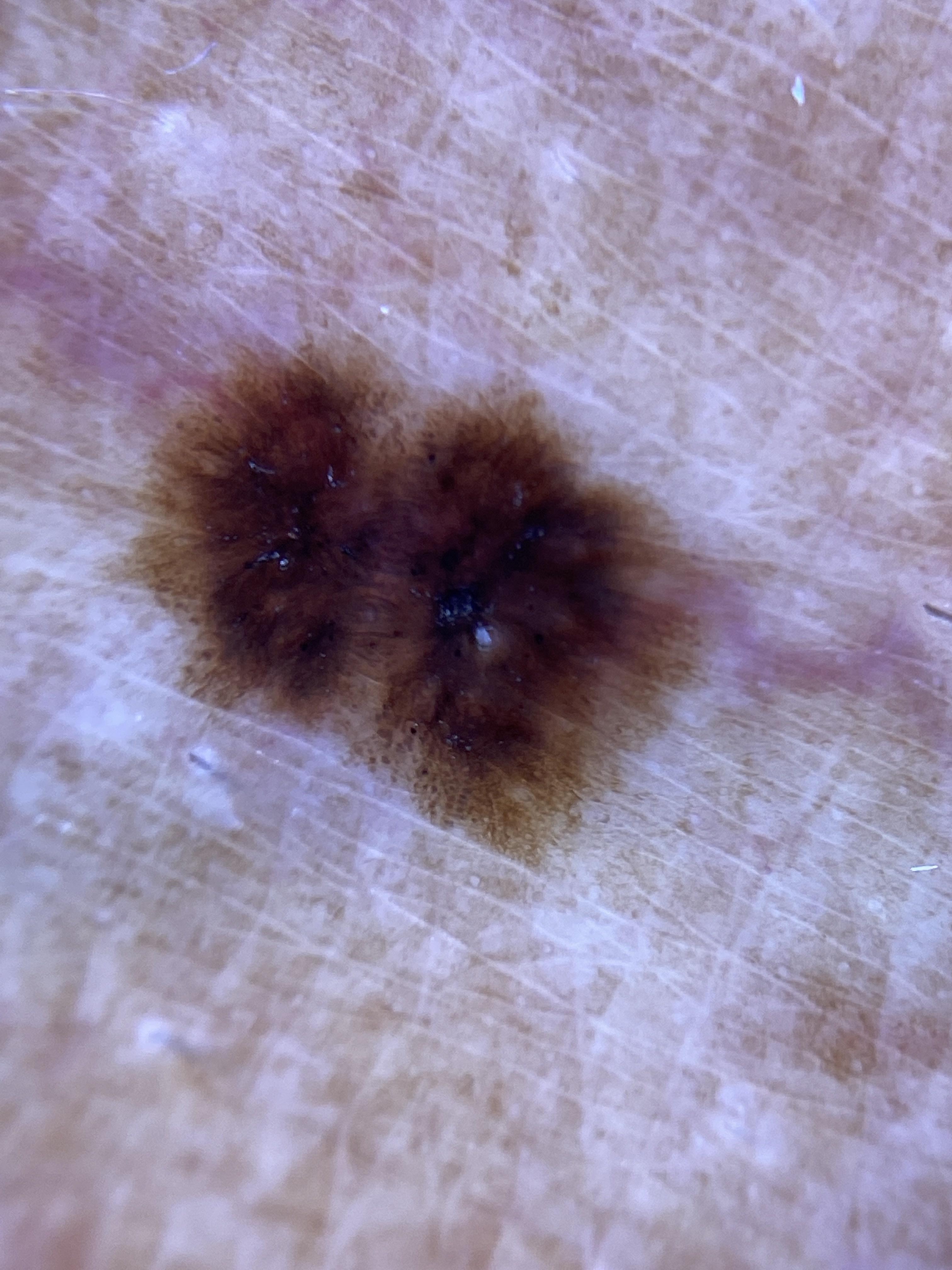Clinical context: A male patient aged 68-72. The lesion involves a lower extremity. Diagnosis: Histopathologically confirmed as a benign lesion — a nevus.